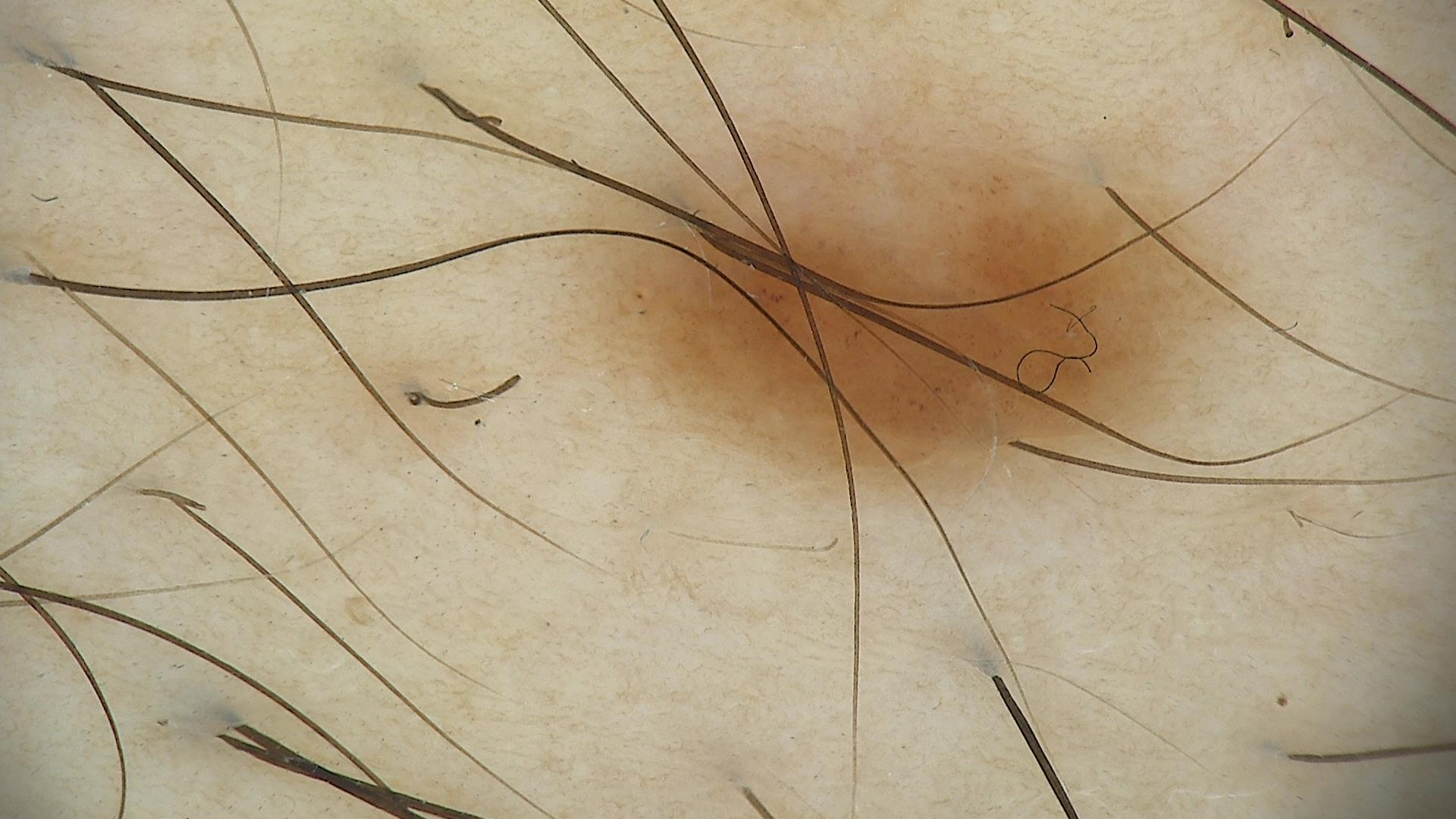<case>
  <image>dermoscopy</image>
  <diagnosis>
    <name>dysplastic junctional nevus</name>
    <code>jd</code>
    <malignancy>benign</malignancy>
    <super_class>melanocytic</super_class>
    <confirmation>expert consensus</confirmation>
  </diagnosis>
</case>